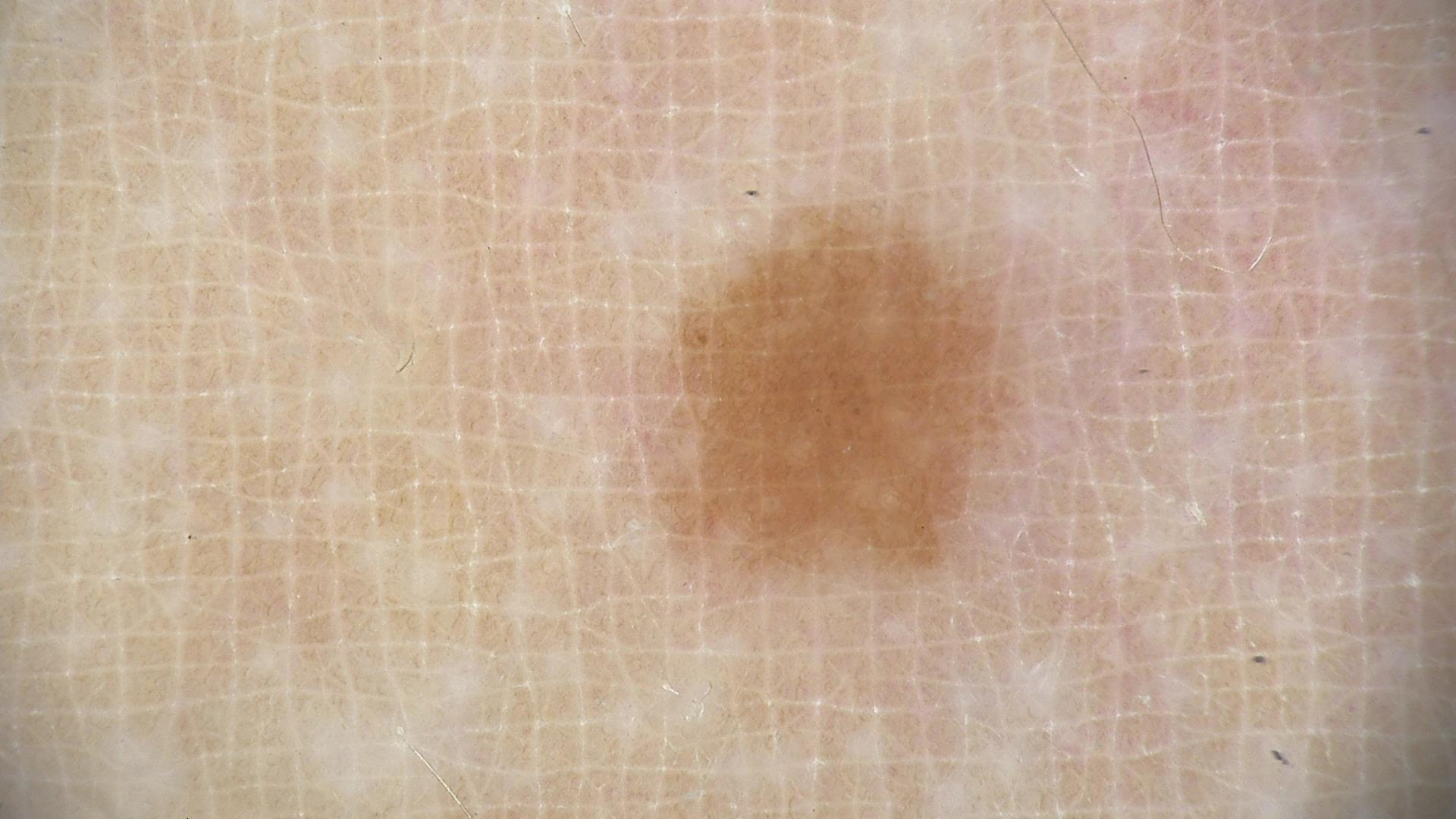class = junctional nevus (expert consensus).